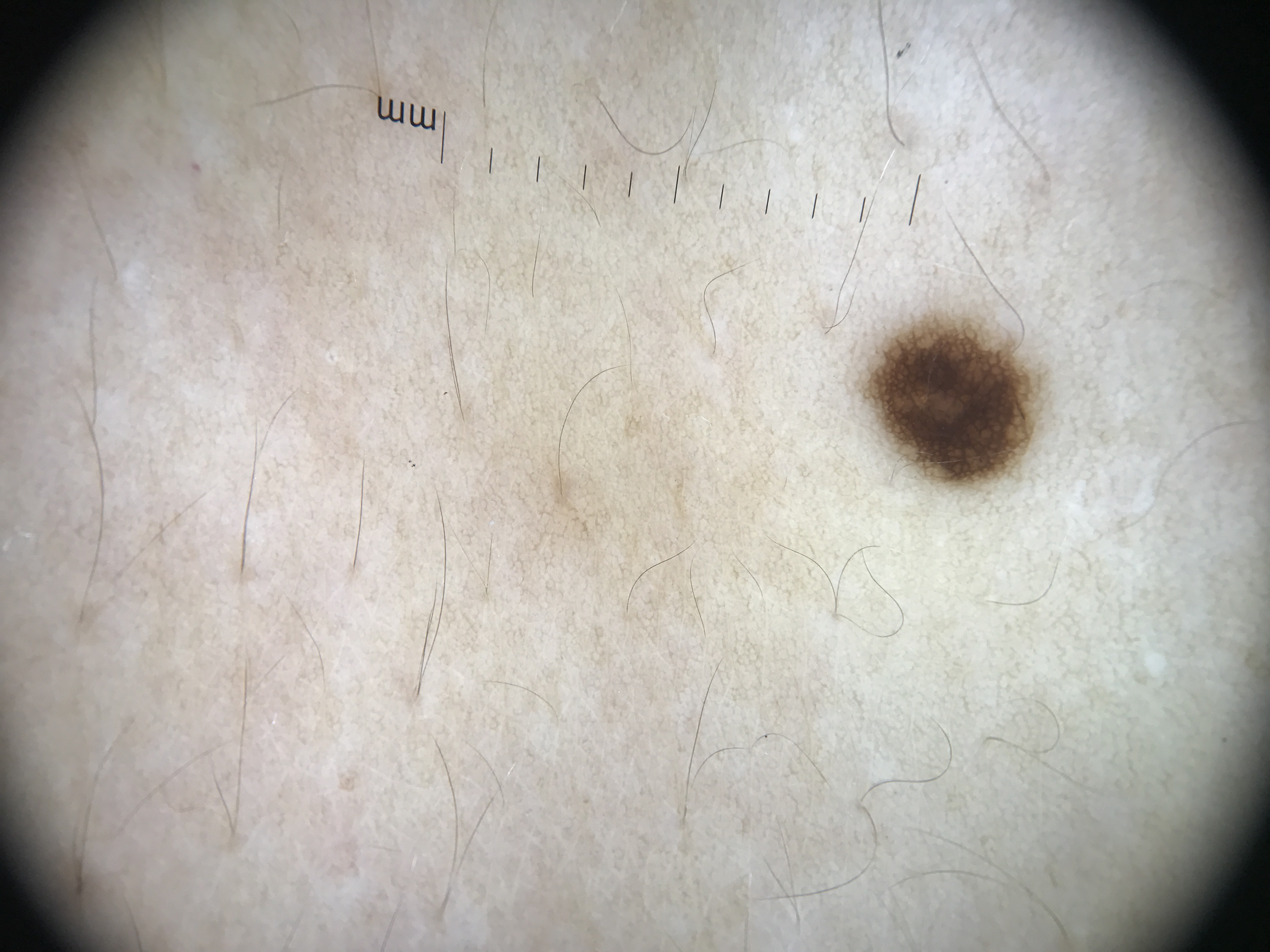Case: A dermoscopic close-up of a skin lesion. Impression: Labeled as a benign lesion — a dysplastic junctional nevus.